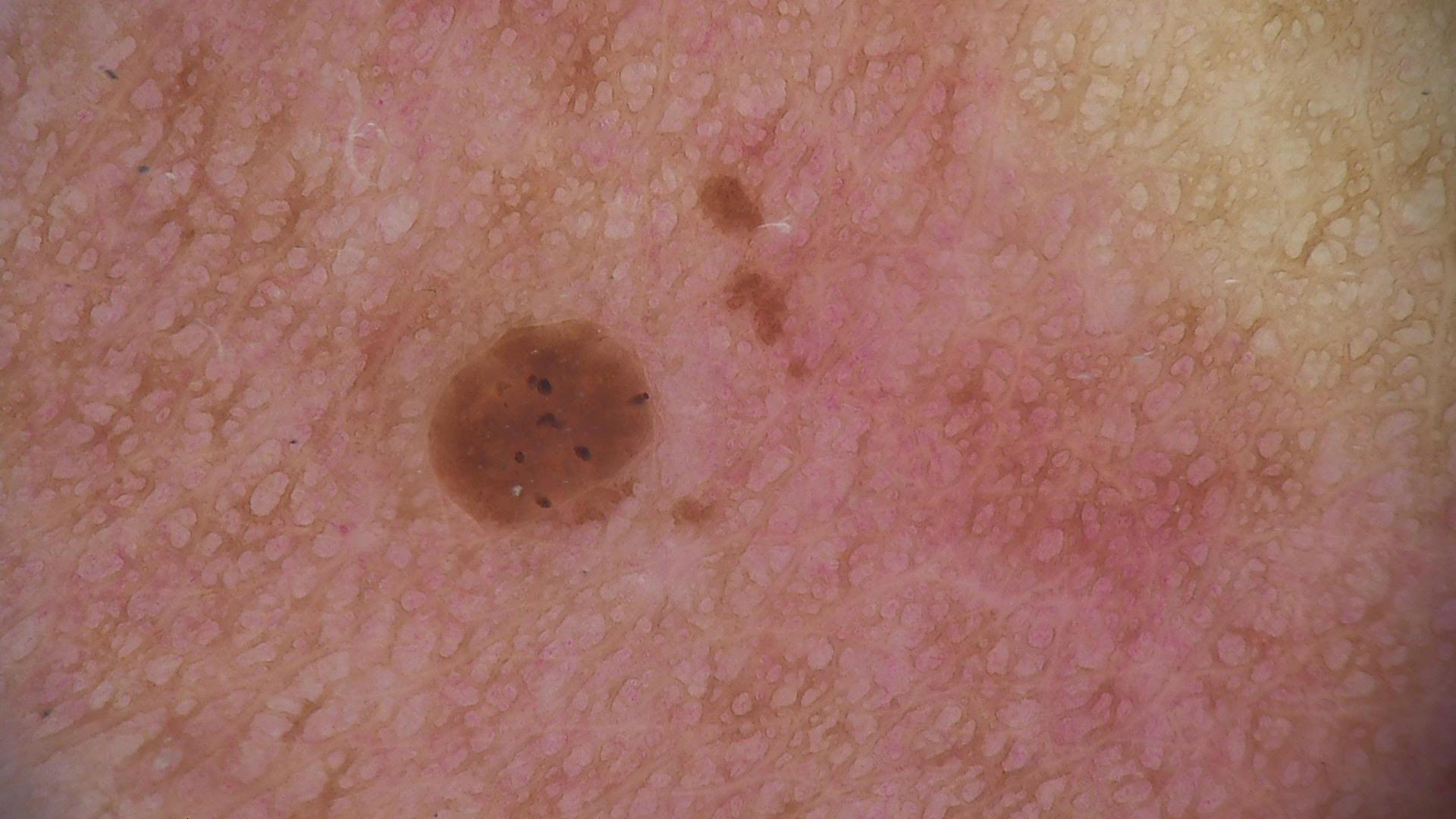The architecture is that of a keratinocytic lesion.
The diagnostic label was a seborrheic keratosis.